Reported duration is less than one week · self-categorized by the patient as a rash · the photo was captured at an angle · male contributor, age 18–29 · located on the head or neck · texture is reported as raised or bumpy · Fitzpatrick II; non-clinician graders estimated Monk skin tone scale 3 (US pool) or 2 (India pool):
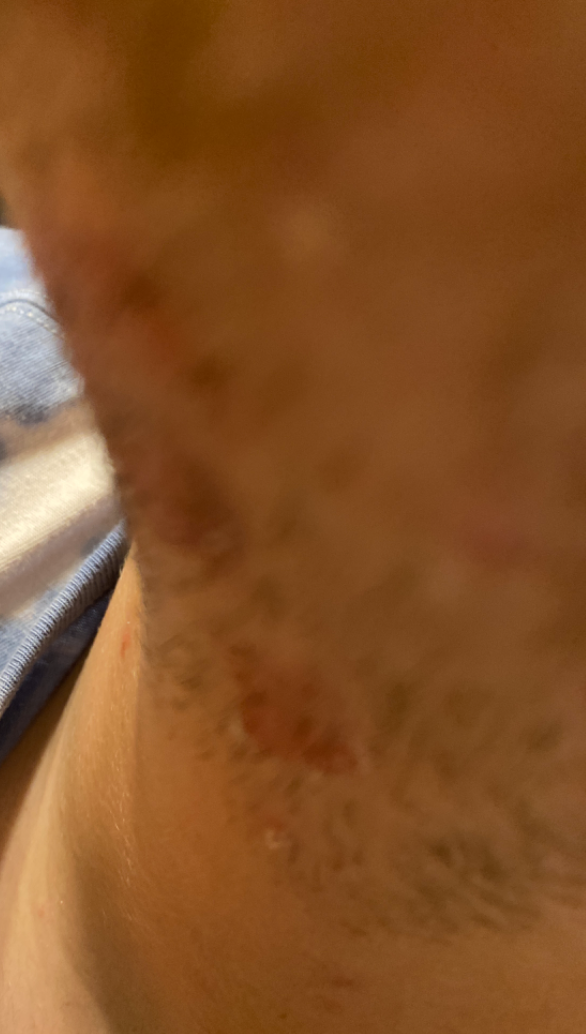clinical impression — Impetigo, Allergic Contact Dermatitis and Irritant Contact Dermatitis were considered with similar weight